A skin lesion imaged with a dermatoscope. Collected as part of a research study, without a referral diagnosis: 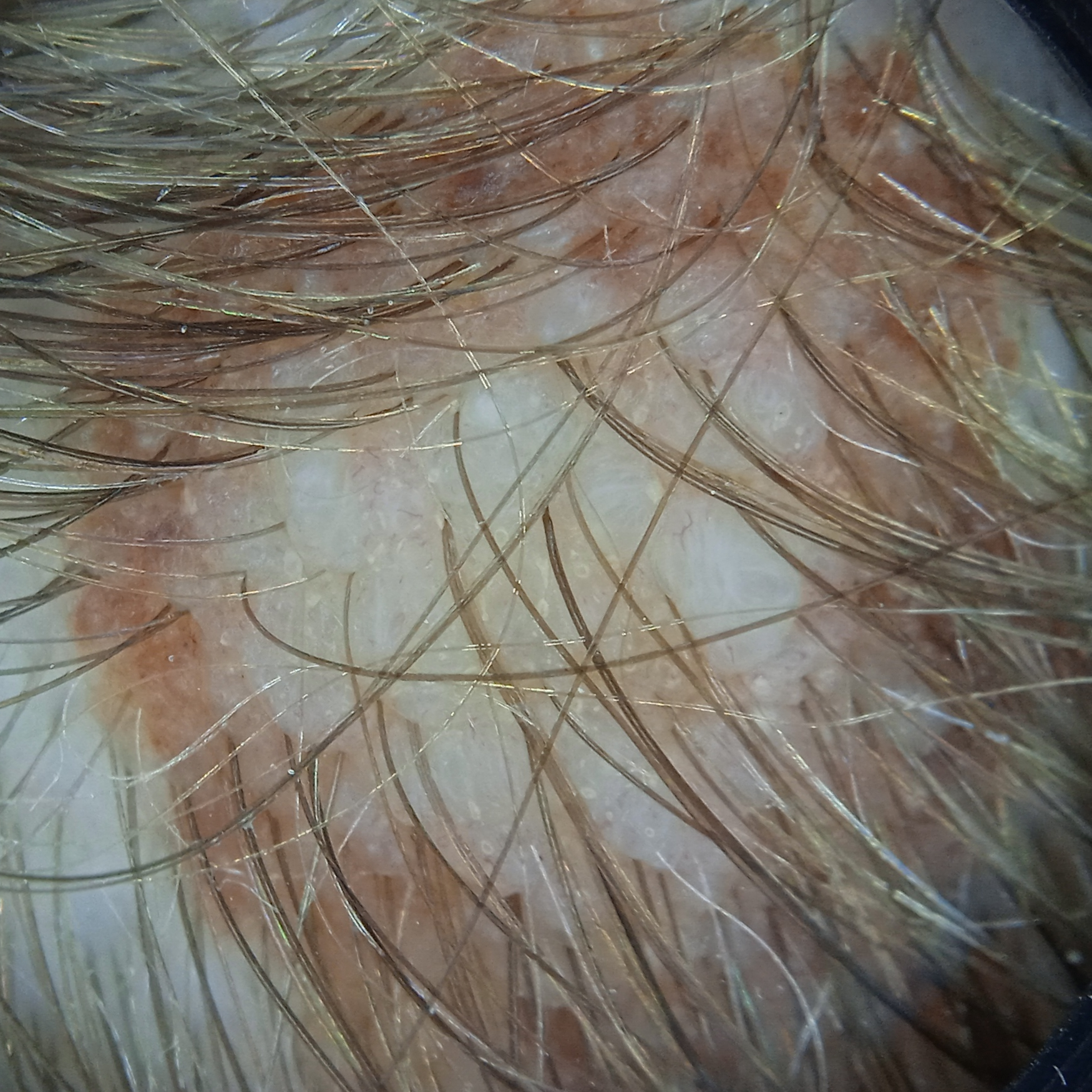Findings:
The lesion is located on the head. The lesion measures approximately 9.1 mm.
Conclusion:
The lesion was assessed as a melanocytic nevus.